Close-up view.
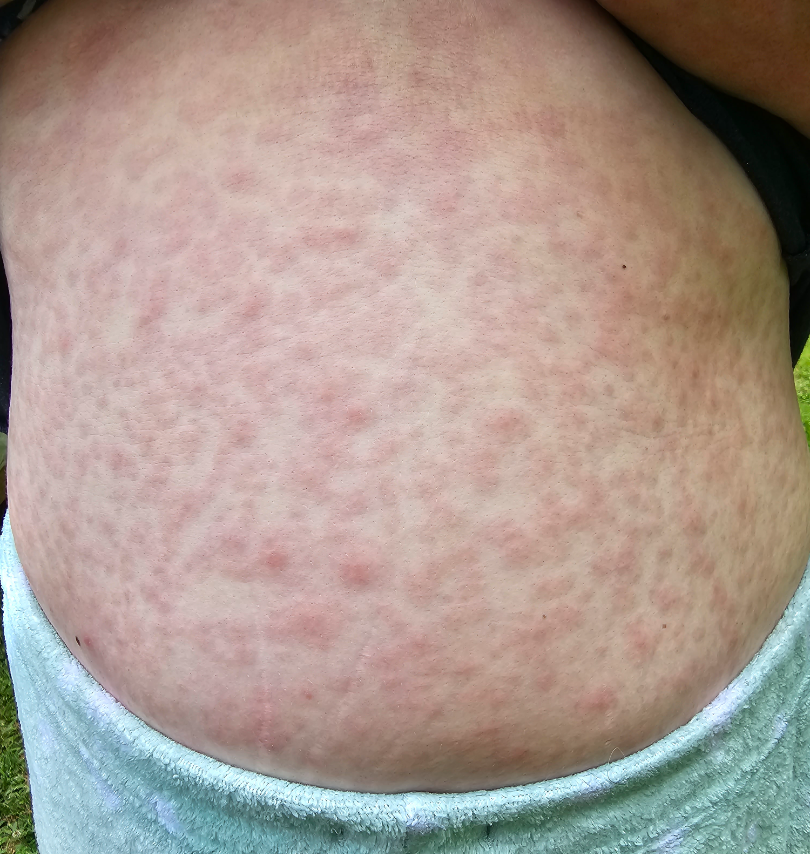assessment: ungradable on photographic review
skin tone: Fitzpatrick skin type III